The patient also reports joint pain and fatigue. Texture is reported as raised or bumpy and fluid-filled. A close-up photograph. The affected area is the arm and leg. Female patient, age 40–49. The patient reports the condition has been present for one to four weeks. The lesion is associated with bothersome appearance and itching. Self-categorized by the patient as a rash.
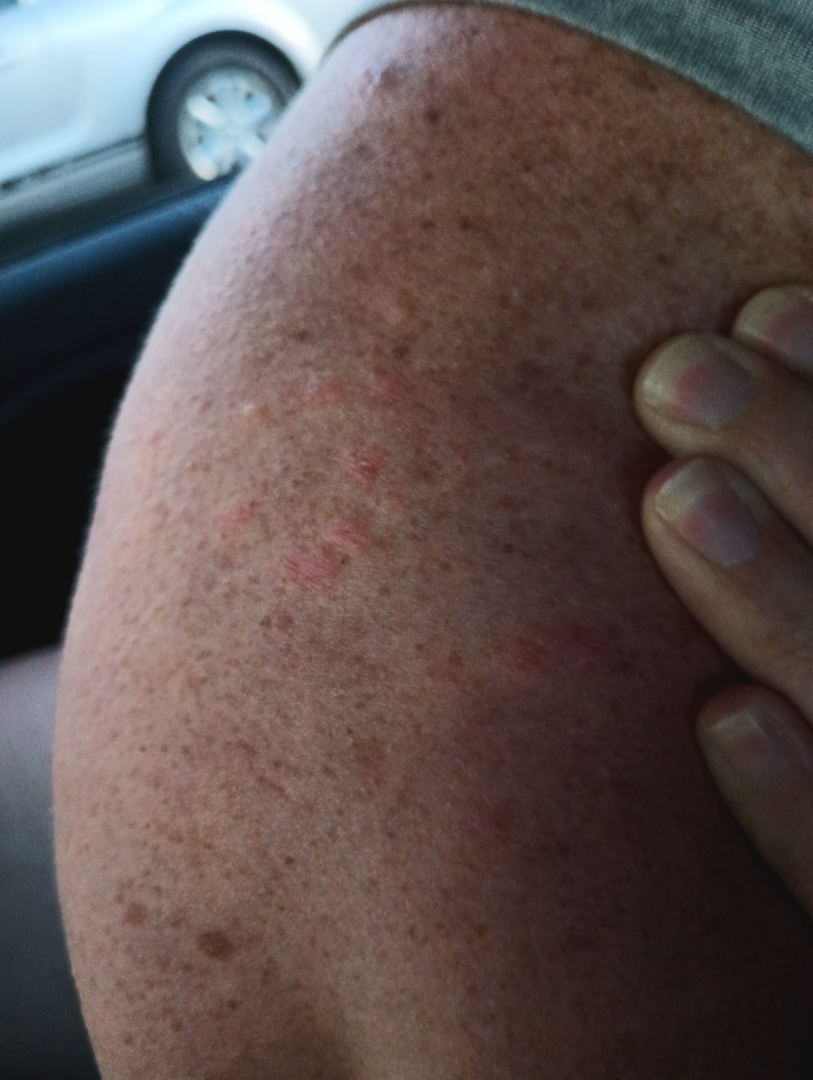Assessment:
The reviewing dermatologist's impression was: Insect Bite (leading); Folliculitis (considered); Eczema (considered).